A dermoscopy image of a single skin lesion:
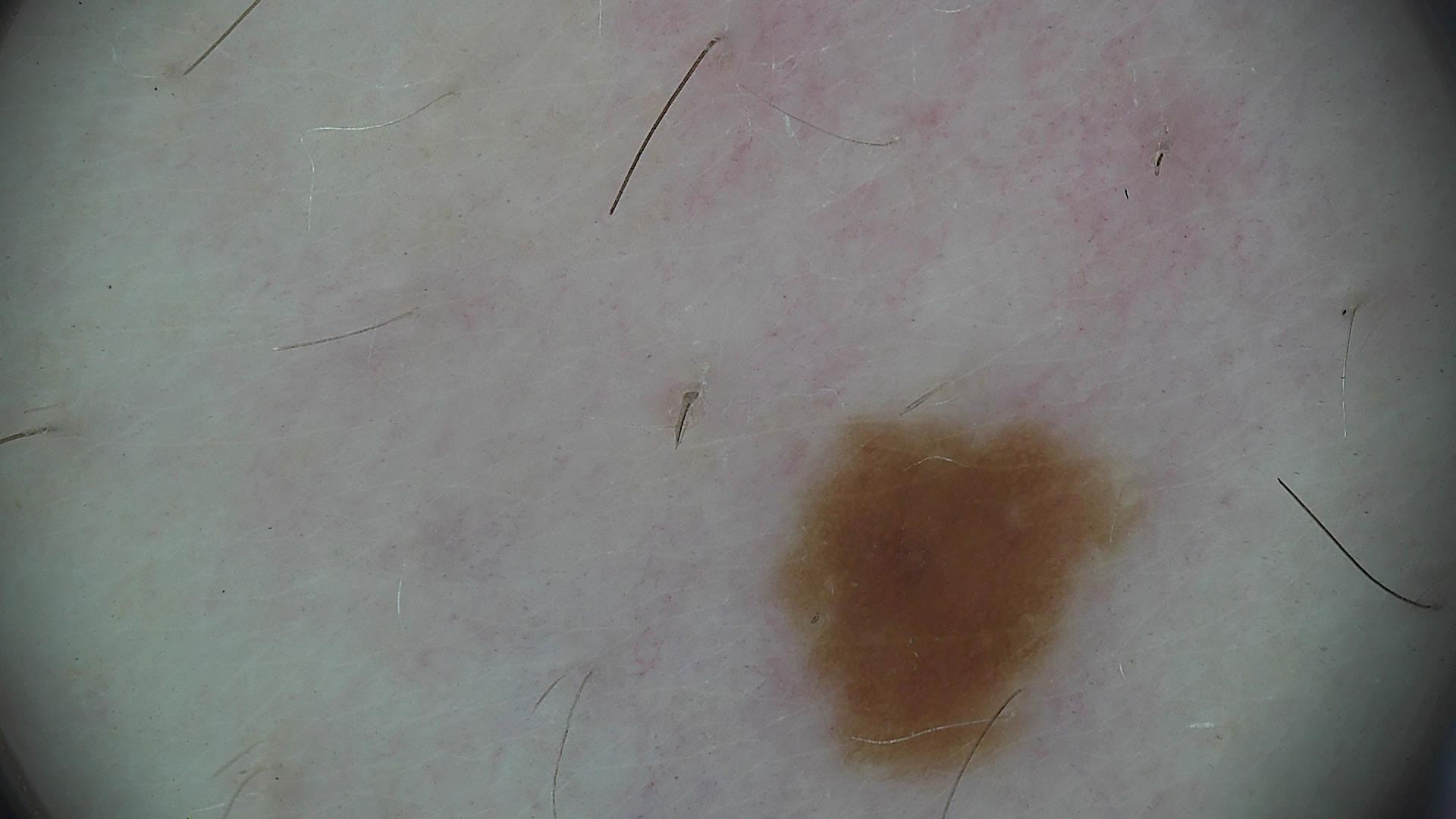Findings: This is a banal lesion. Conclusion: Labeled as a junctional nevus.